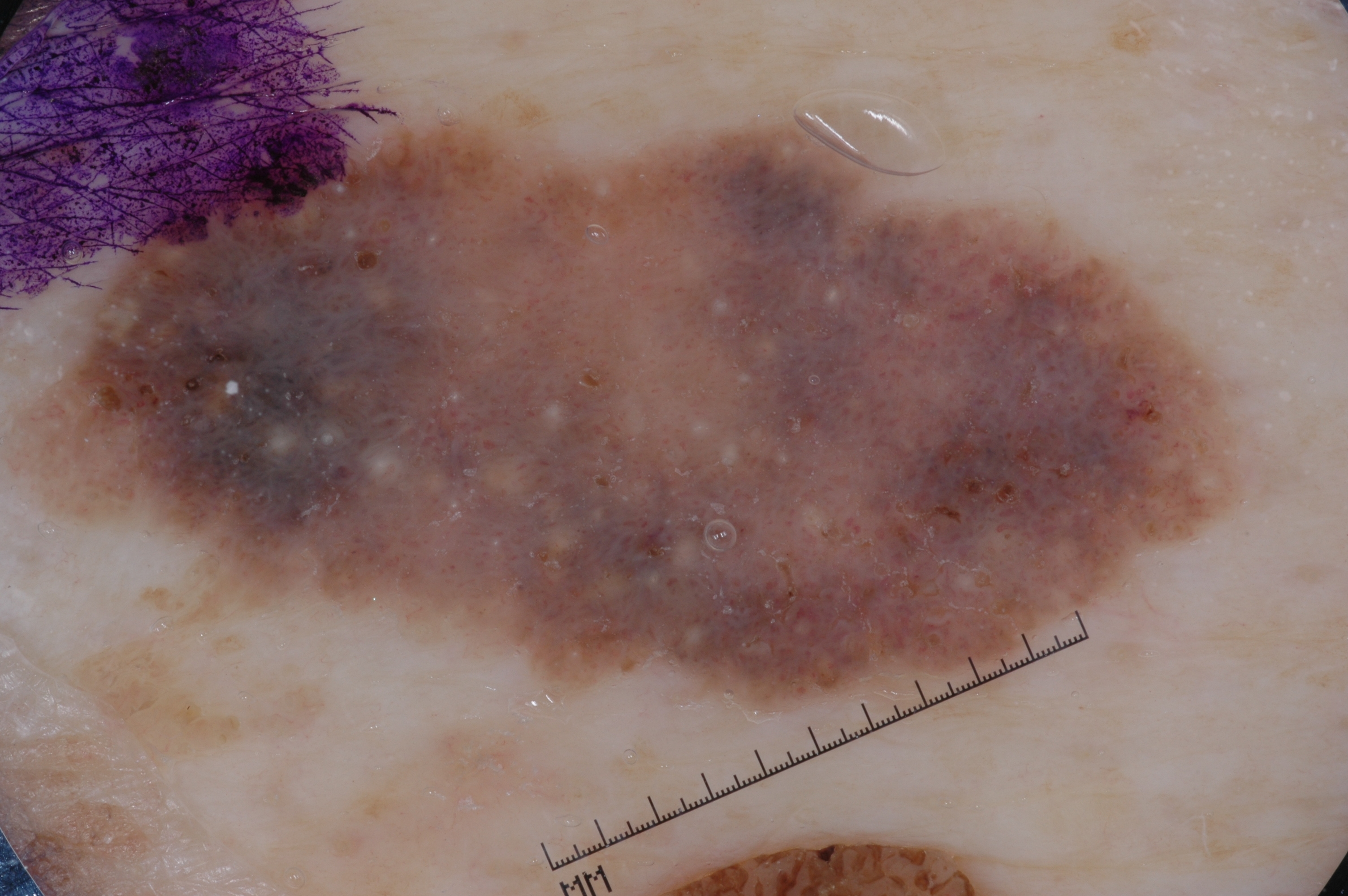  image:
    modality: dermoscopy
  patient:
    sex: male
    age_approx: 85+
  dermoscopic_features:
    present:
      - milia-like cysts
    absent:
      - pigment network
      - streaks
      - negative network
  lesion_location:
    bbox_xyxy:
      - 2
      - 120
      - 1262
      - 723
  diagnosis:
    name: seborrheic keratosis
    malignancy: benign
    lineage: keratinocytic
    provenance: clinical